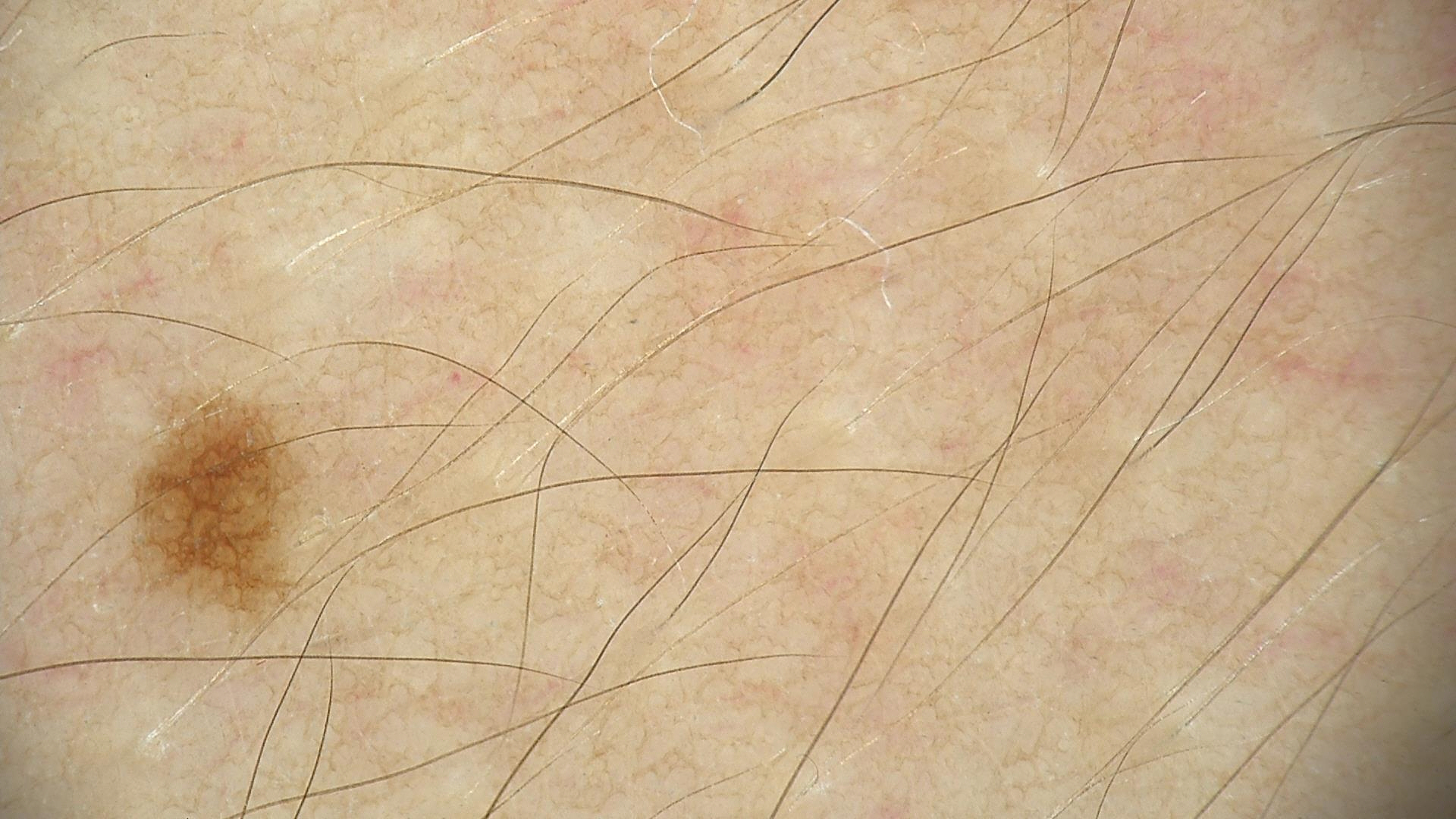Case:
• image — dermatoscopy
• assessment — junctional nevus (expert consensus)